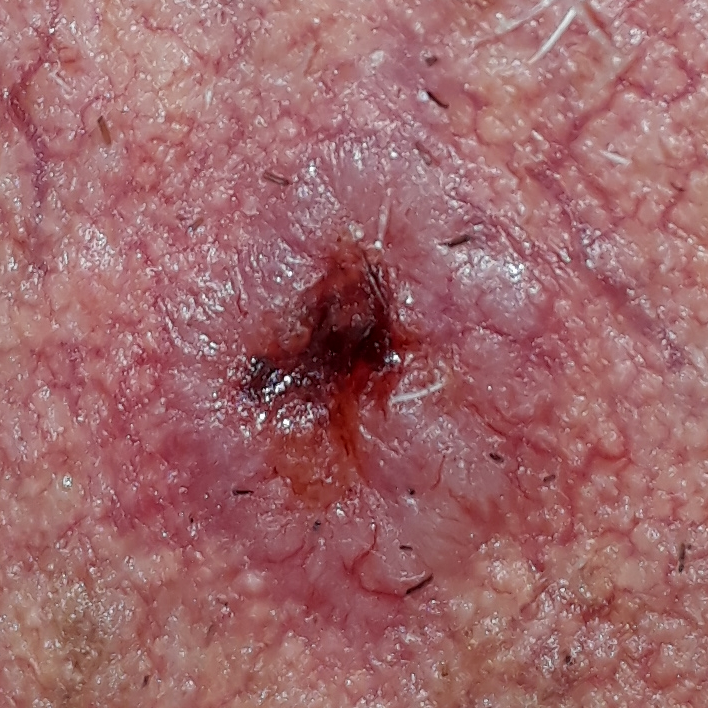A male patient in their mid-80s.
A smartphone photograph of a skin lesion.
The lesion was found on the face.
Per patient report, the lesion itches, is elevated, hurts, has grown, and has bled.
On biopsy, the diagnosis was a basal cell carcinoma.